Dermoscopy of a skin lesion.
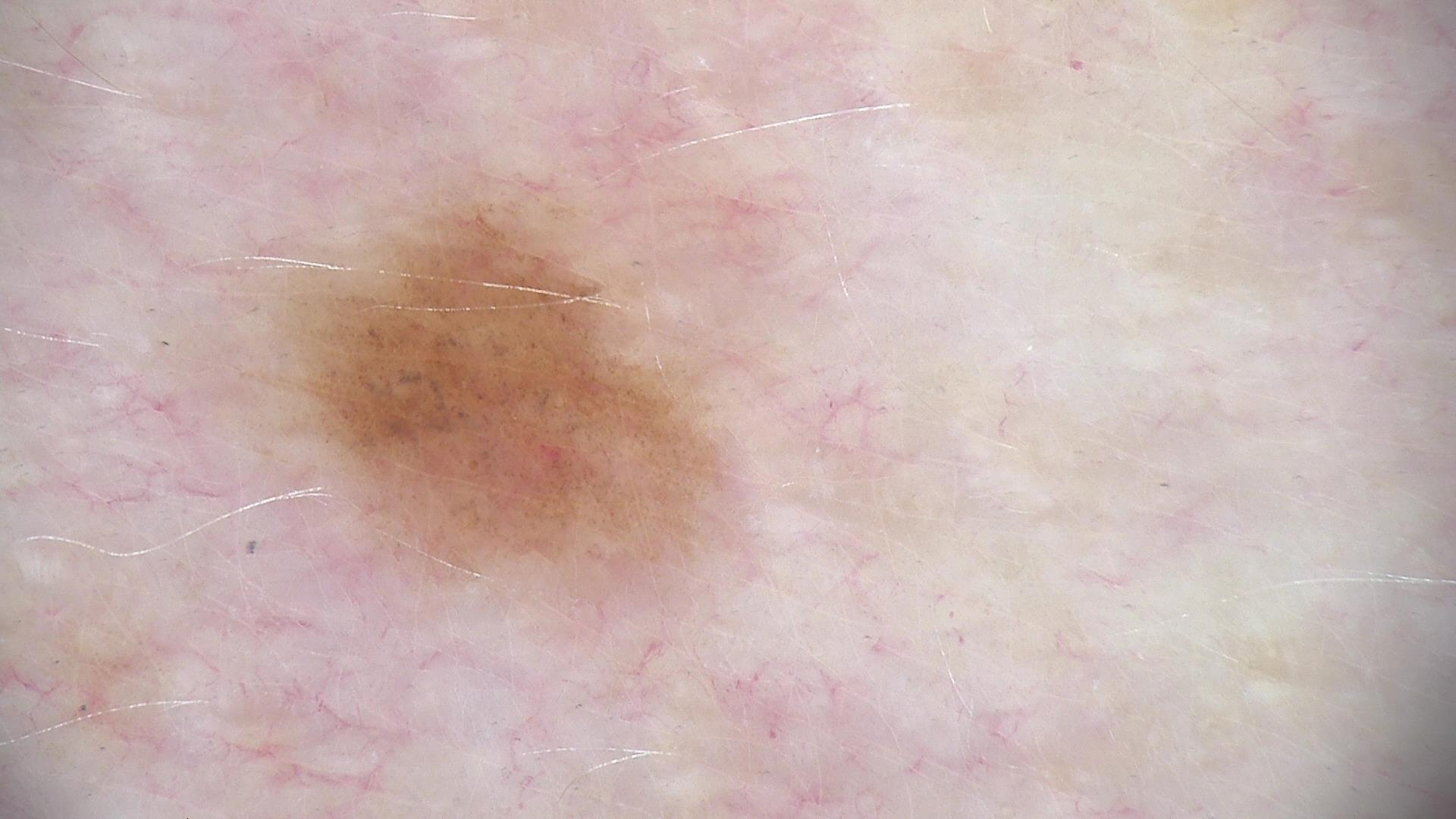label: dysplastic junctional nevus (expert consensus).